The photo was captured at a distance. The affected area is the leg, head or neck and arm — 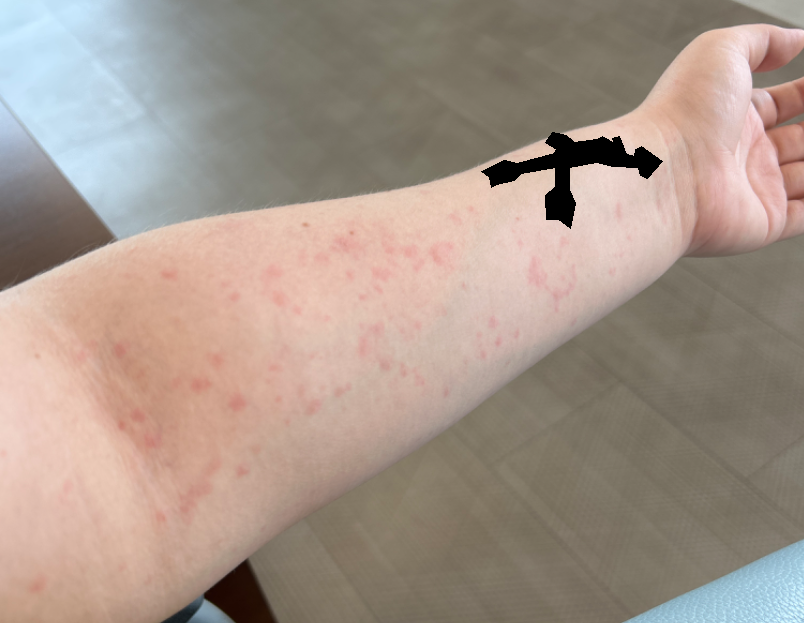Q: Could the case be diagnosed?
A: unable to determine
Q: When did this start?
A: about one day
Q: Patient's own categorization?
A: a rash
Q: What is the lesion texture?
A: raised or bumpy
Q: Reported symptoms?
A: burning and itching